Present for three to twelve months. The patient considered this a rash. Texture is reported as rough or flaky and raised or bumpy. No associated systemic symptoms reported. Reported lesion symptoms include itching, enlargement, darkening, burning and bothersome appearance. Located on the leg. Female contributor, age 18–29. The photograph was taken at a distance.
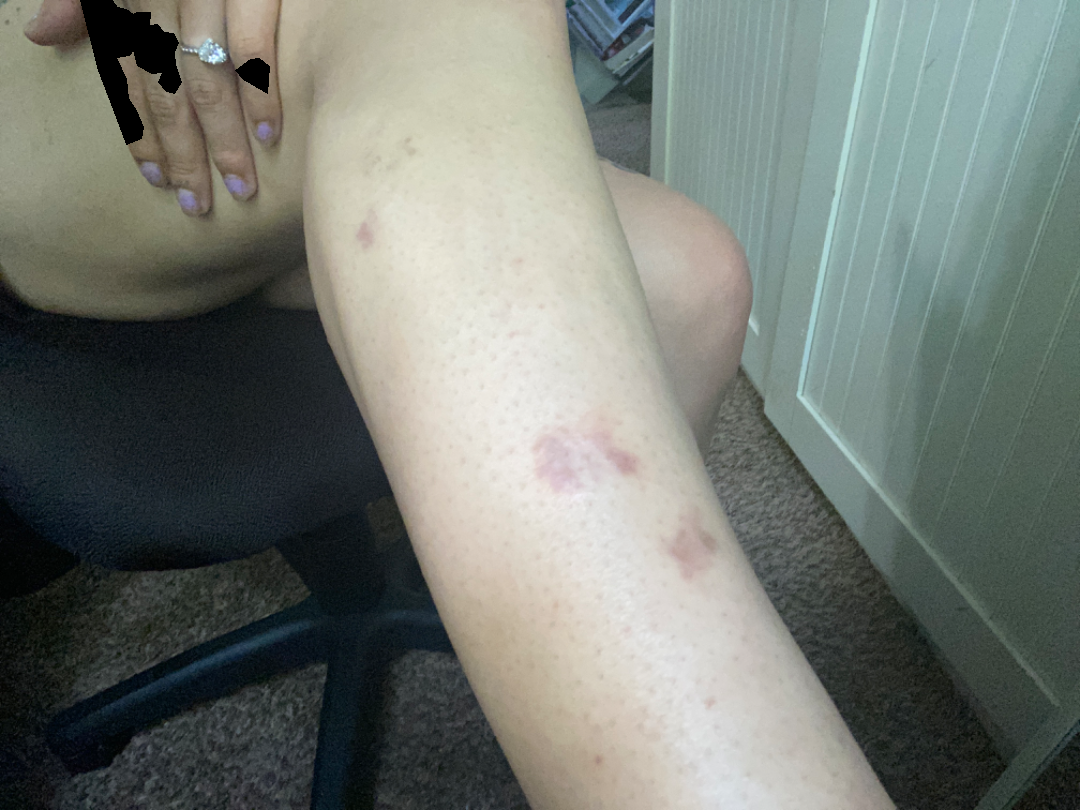The reviewer was unable to grade this case for skin condition.